A dermoscopic close-up of a skin lesion.
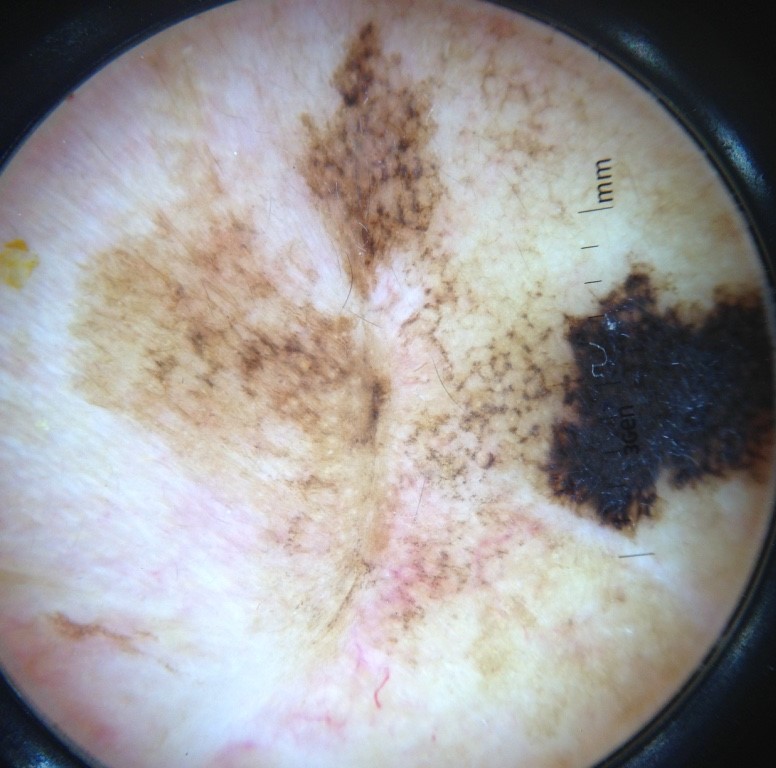Case:
* pathology: lentigo maligna (biopsy-proven)